A patient 39 years old; a smartphone photograph of a skin lesion — 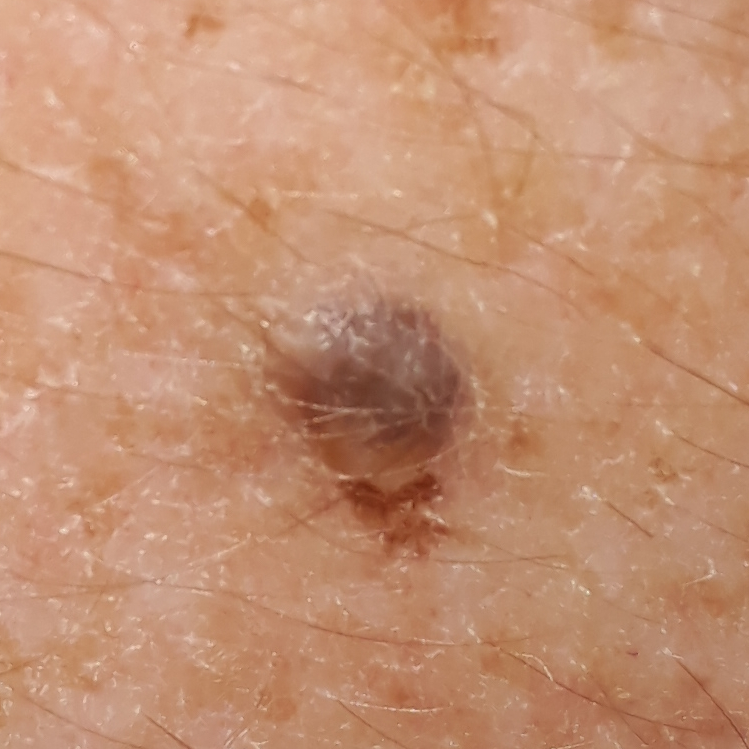Q: What is the anatomic site?
A: a forearm
Q: Any reported symptoms?
A: growth, elevation / no change in appearance
Q: What is the diagnosis?
A: nevus (clinical consensus)